A male patient aged 13 to 17 · a dermoscopic image of a skin lesion: 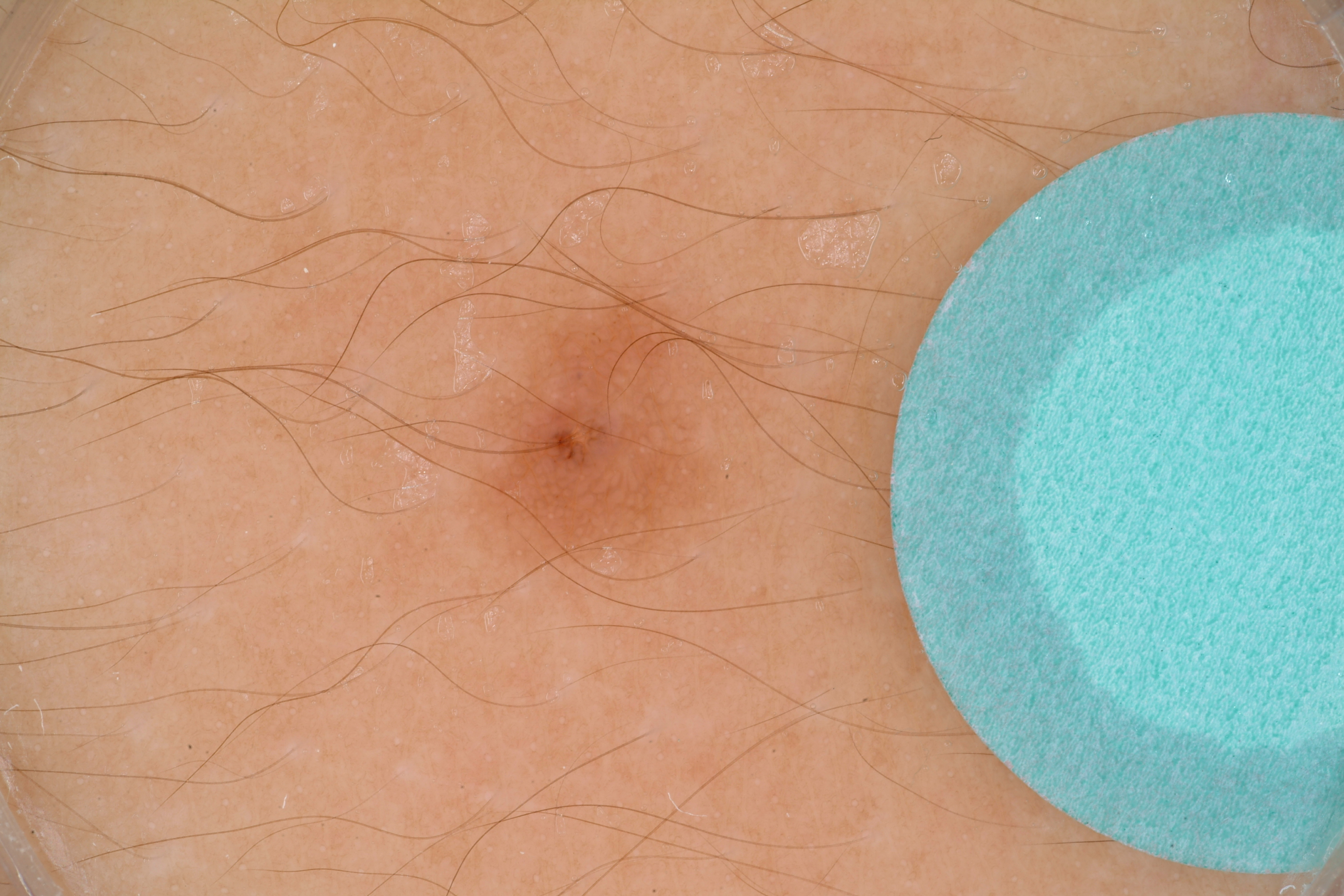With coordinates (x1, y1, x2, y2), the lesion occupies the region (433, 285, 743, 607). Dermoscopy demonstrates pigment network. Consistent with a melanocytic nevus.